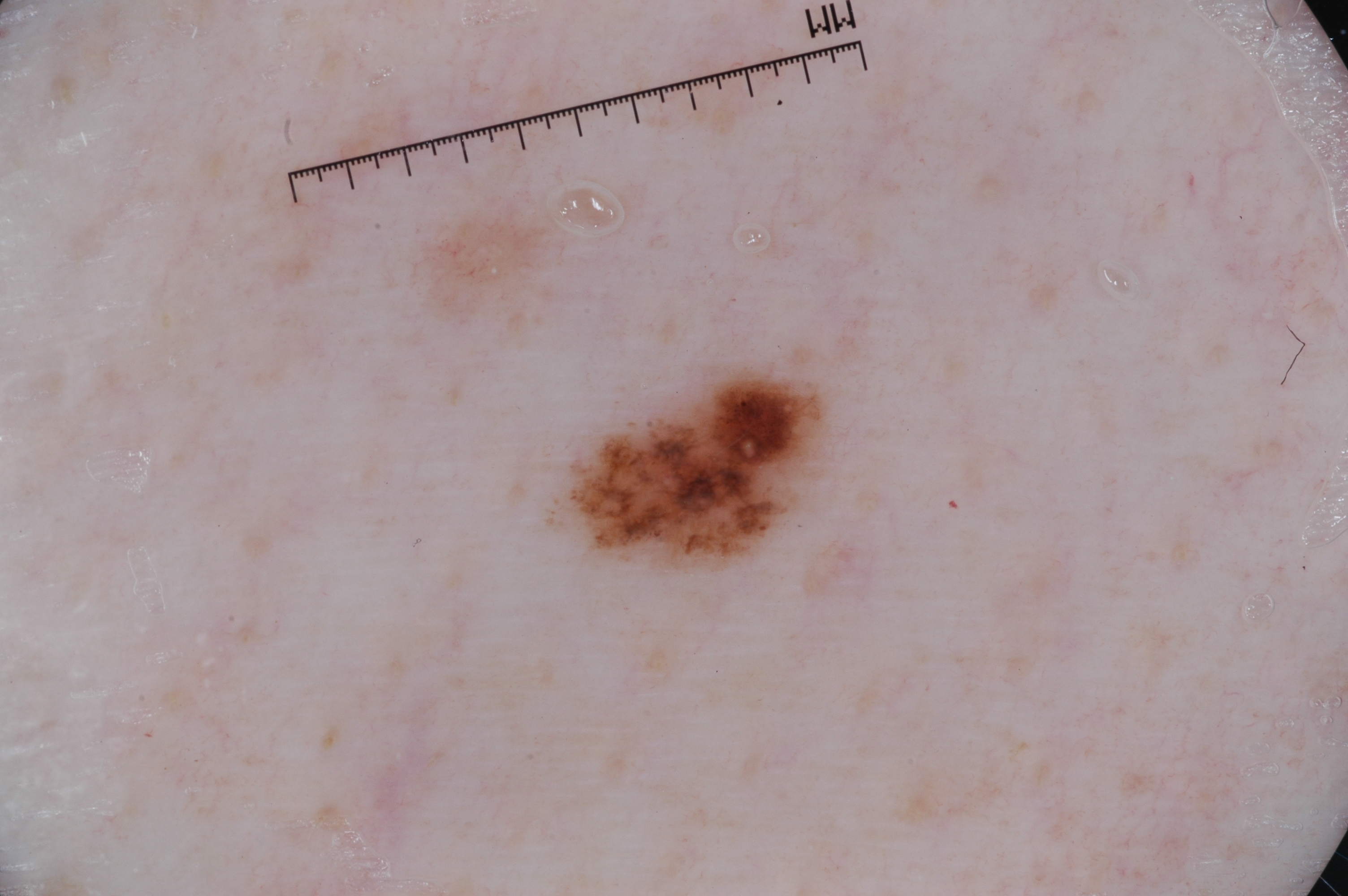Findings: A skin lesion imaged with a dermatoscope. With coordinates (x1, y1, x2, y2), the lesion is bounded by 552/362/833/573. The lesion occupies roughly 3% of the field. Dermoscopic review identifies milia-like cysts; no streaks, negative network, or pigment network. Impression: The lesion was assessed as a melanocytic nevus, a benign lesion.